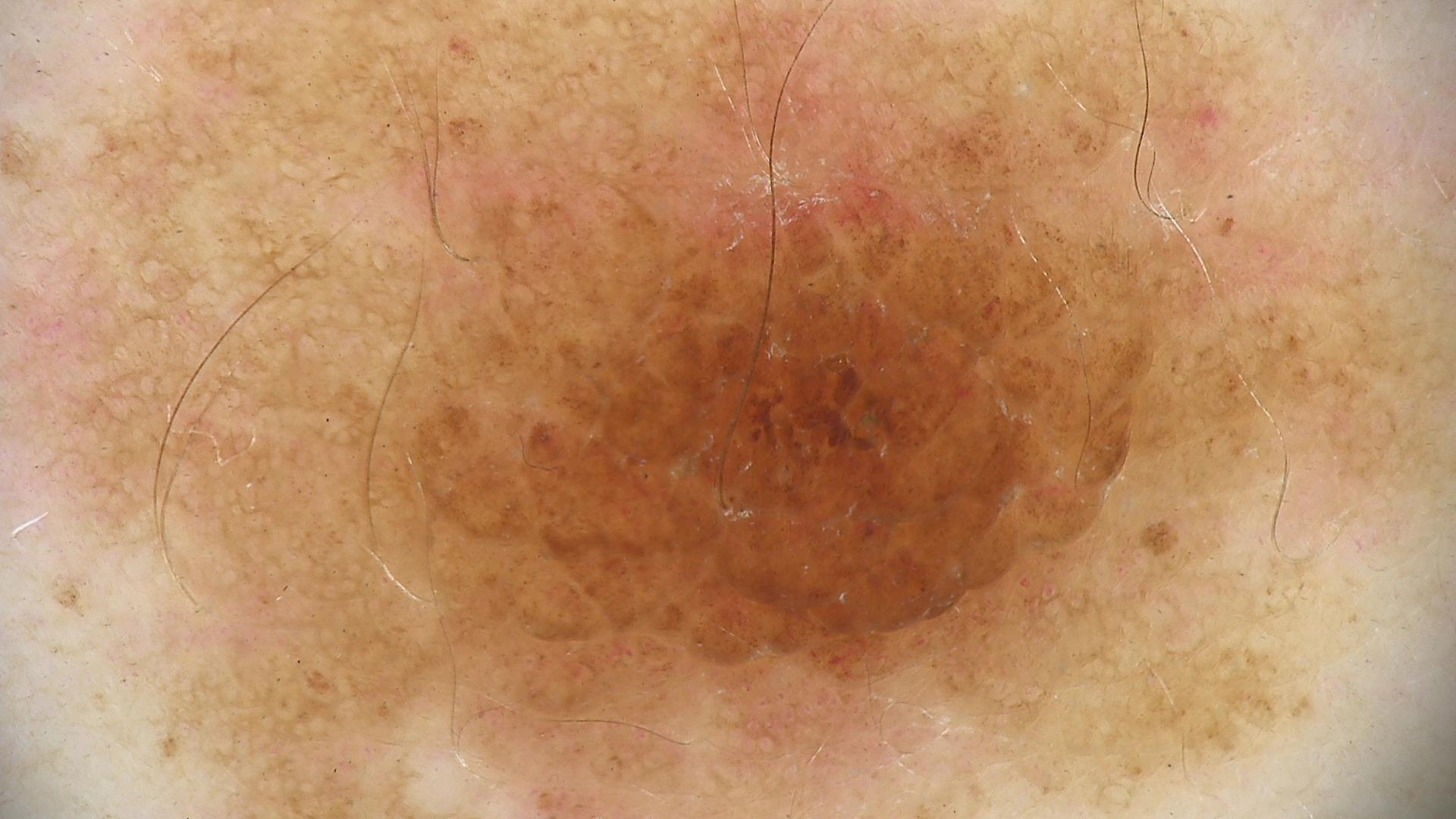imaging = dermatoscopy | diagnostic label = compound nevus (expert consensus).